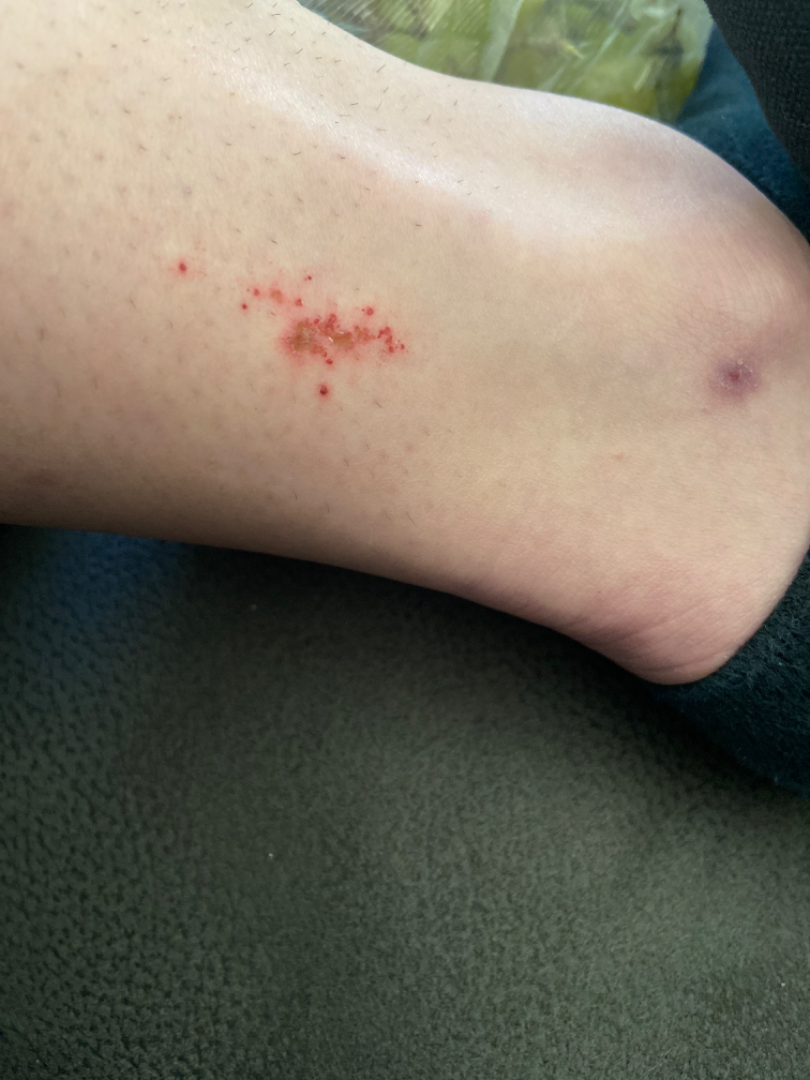* assessment · could not be assessed
* surface texture · raised or bumpy
* skin tone · Fitzpatrick phototype III
* patient describes the issue as · a rash
* body site · leg
* view · close-up
* present for · less than one week